The photograph was taken at an angle · the lesion involves the top or side of the foot and leg.
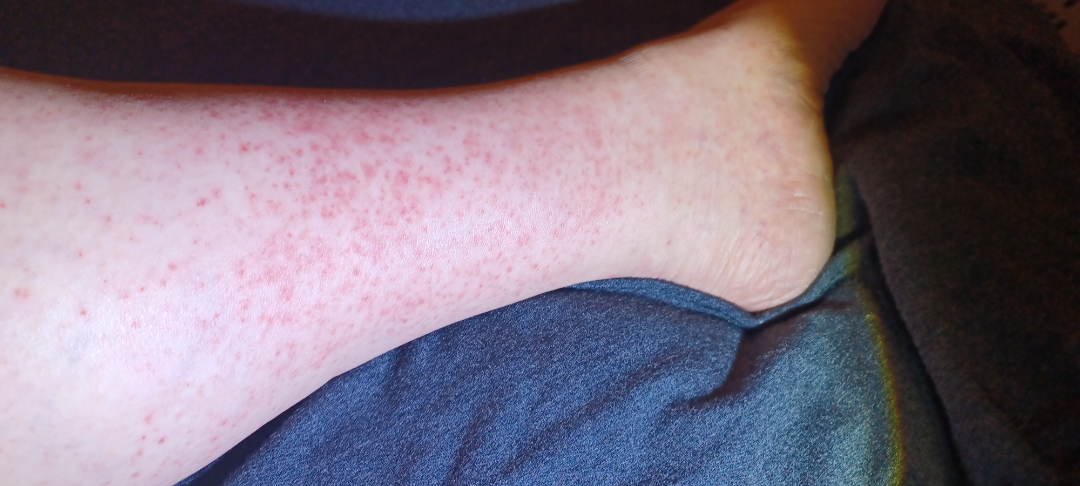No associated systemic symptoms reported. Skin tone: FST II. Reported duration is about one day. Symptoms reported: burning, bothersome appearance, itching, darkening and enlargement. Self-categorized by the patient as a rash. The lesion is described as flat. On dermatologist assessment of the image: the differential is split between Pigmented purpuric eruption and Leukocytoclastic Vasculitis.